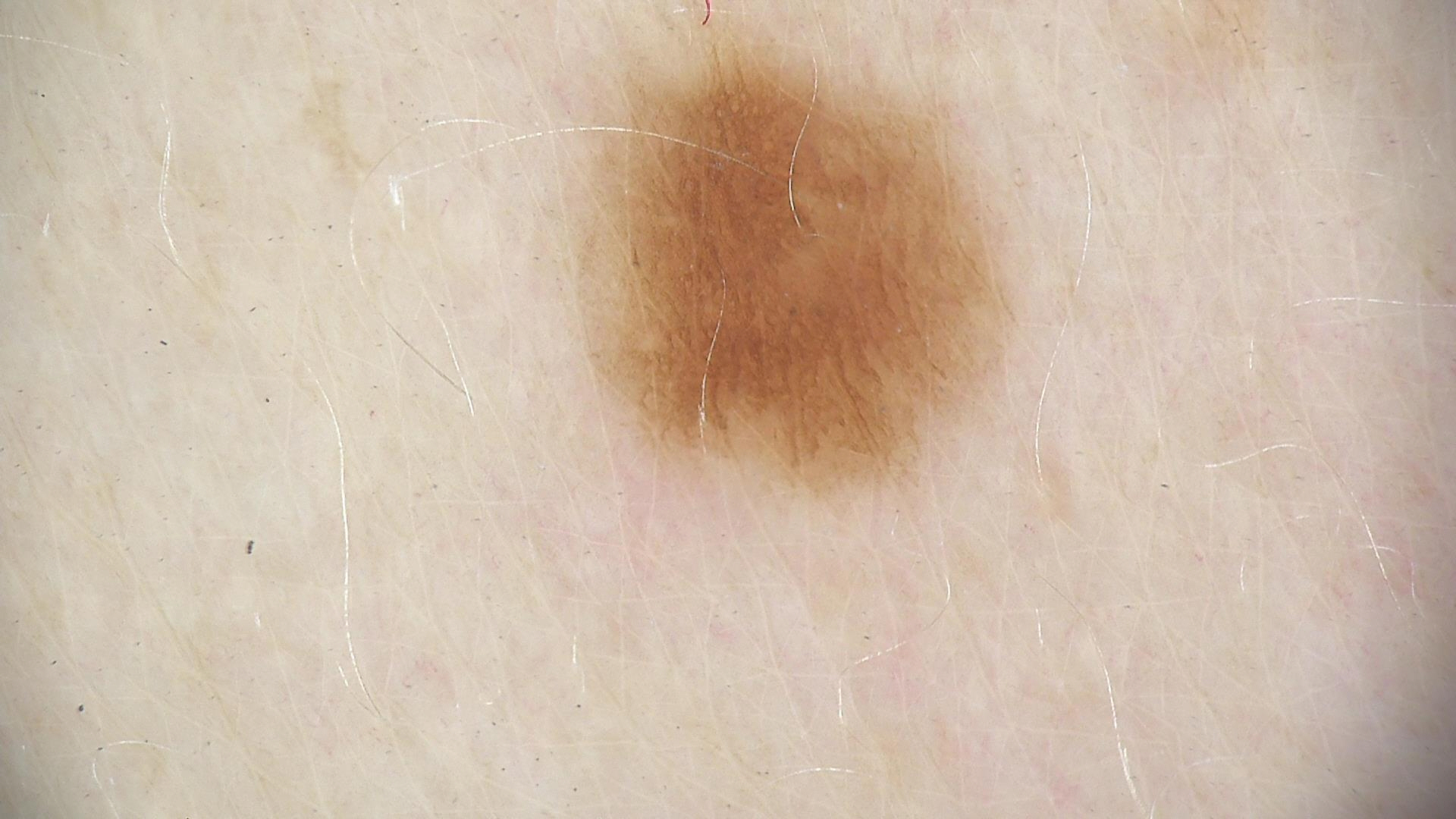Findings:
• assessment: dysplastic junctional nevus (expert consensus)